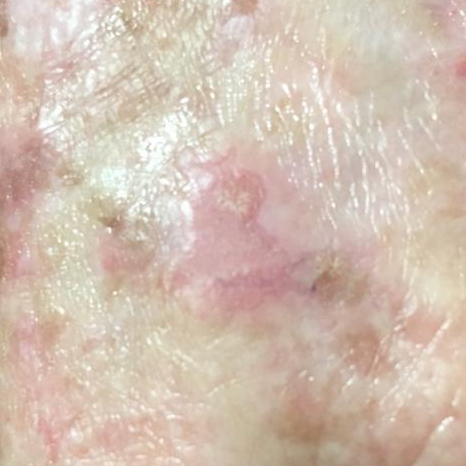Q: Patient demographics?
A: female, age 53
Q: What is the patient's skin type?
A: II
Q: Any relevant history?
A: prior skin cancer (patient or family)
Q: What is the anatomic site?
A: a hand
Q: What are the lesion's dimensions?
A: approx. 7 × 6 mm
Q: What did the workup show?
A: basal cell carcinoma (biopsy-proven)